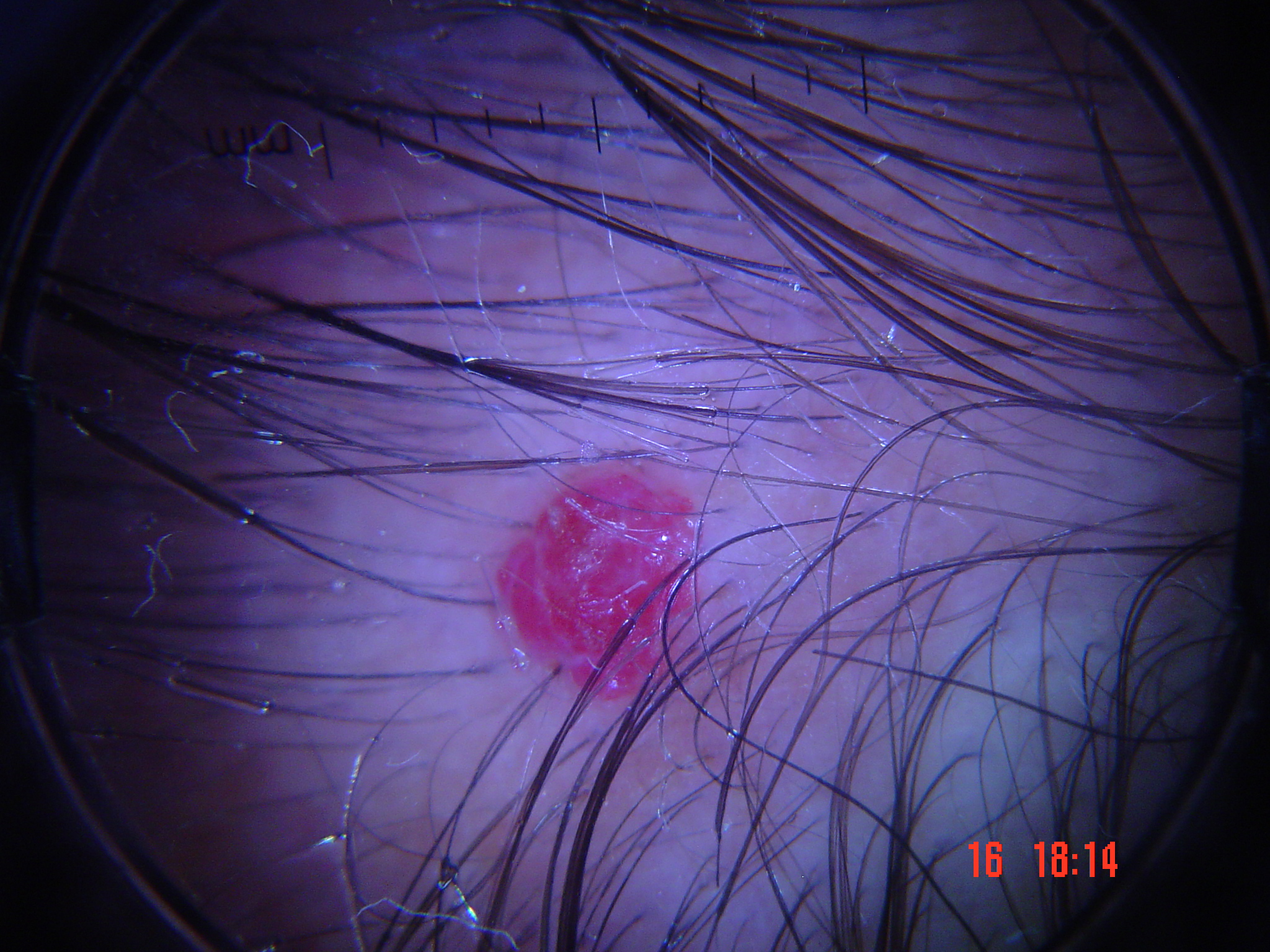  image: dermatoscopy
  diagnosis:
    name: hemangioma
    code: ha
    malignancy: benign
    super_class: non-melanocytic
    confirmation: expert consensus